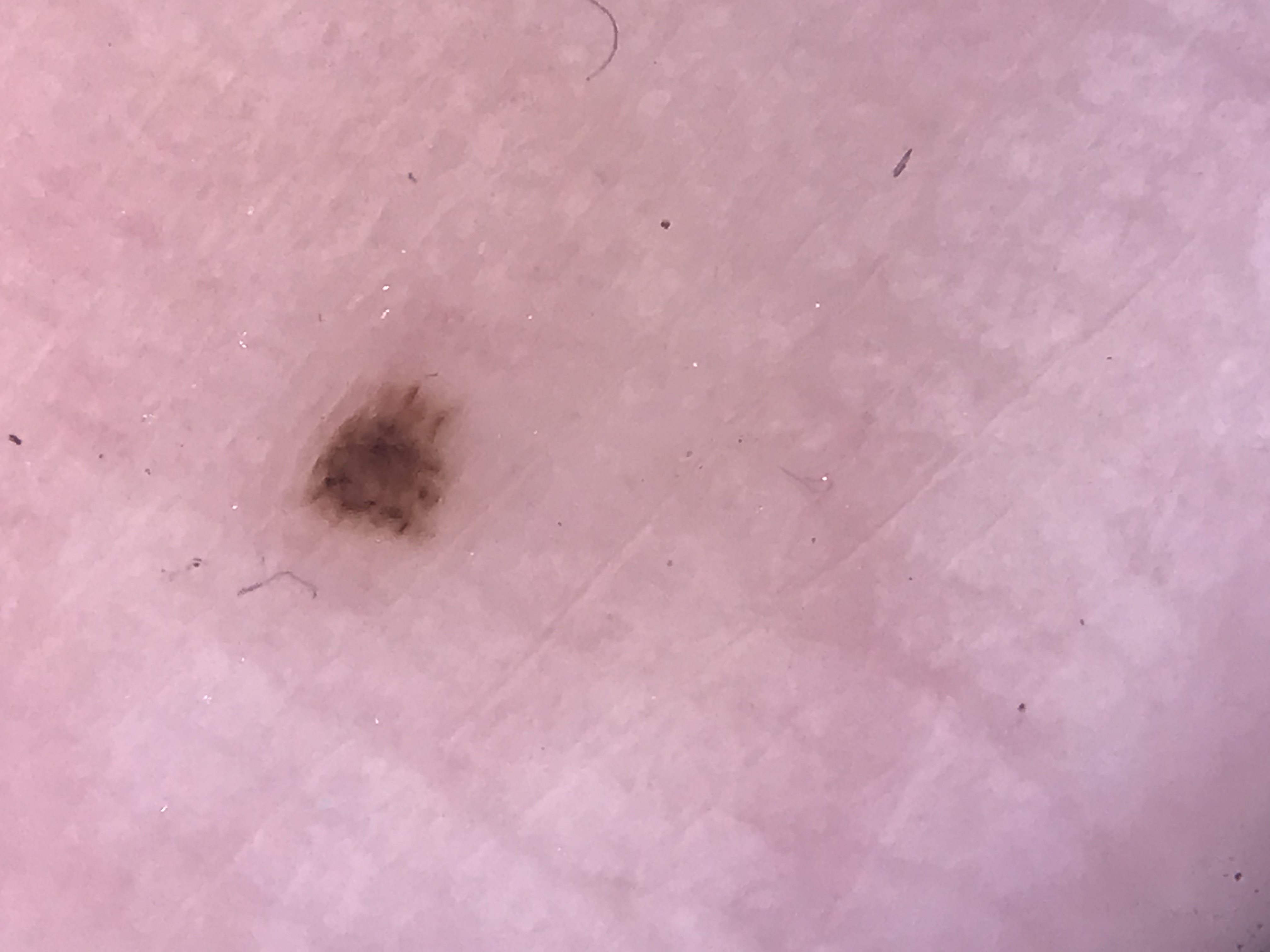Consistent with an acral dysplastic junctional nevus.